The photograph was taken at an angle; the contributor is female; the affected area is the front of the torso and back of the torso — 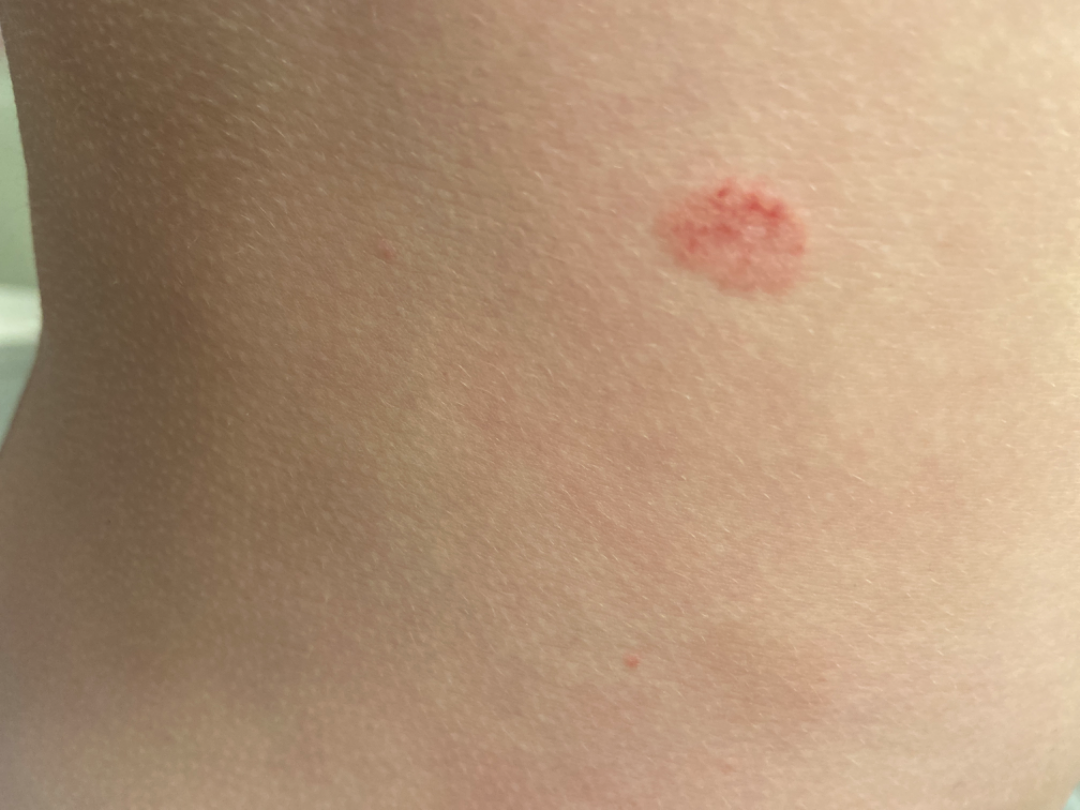Q: What is the differential diagnosis?
A: Pityriasis rosea (primary); Psoriasis (possible); Eczema (less likely)